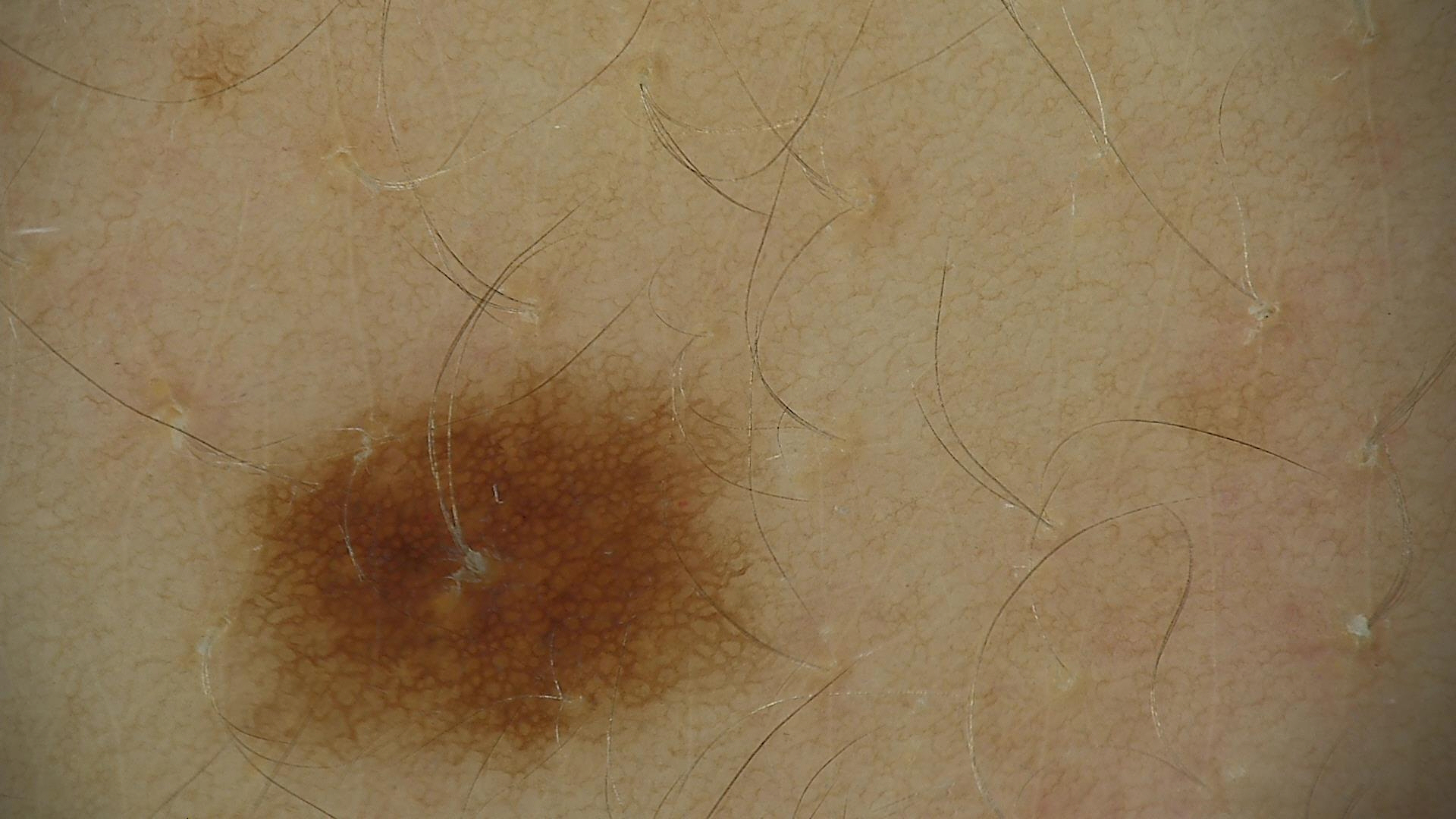Conclusion: Classified as a benign lesion — a dysplastic junctional nevus.